This is a close-up image, the affected area is the arm and back of the torso — 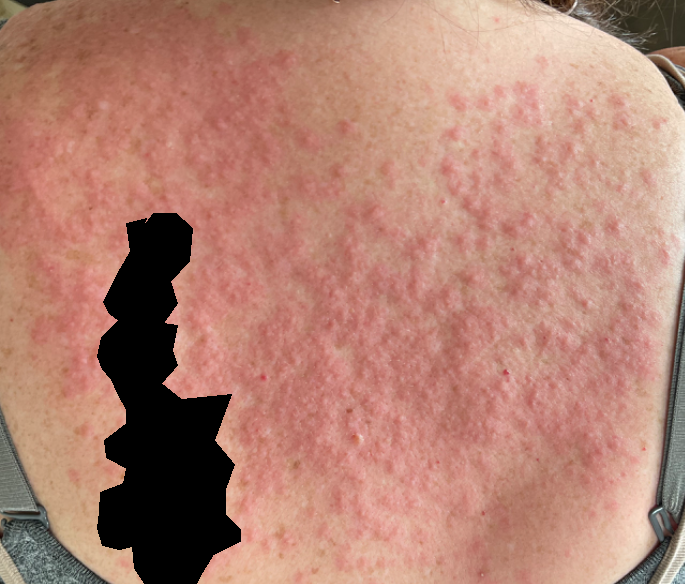Clinical context: Reported lesion symptoms include bothersome appearance. The patient reports the lesion is raised or bumpy. The patient reports the condition has been present for less than one week. Skin tone: Fitzpatrick phototype II. Assessment: On photographic review by a dermatologist: most likely Allergic Contact Dermatitis; also consider Photodermatitis; less likely is Hypersensitivity.